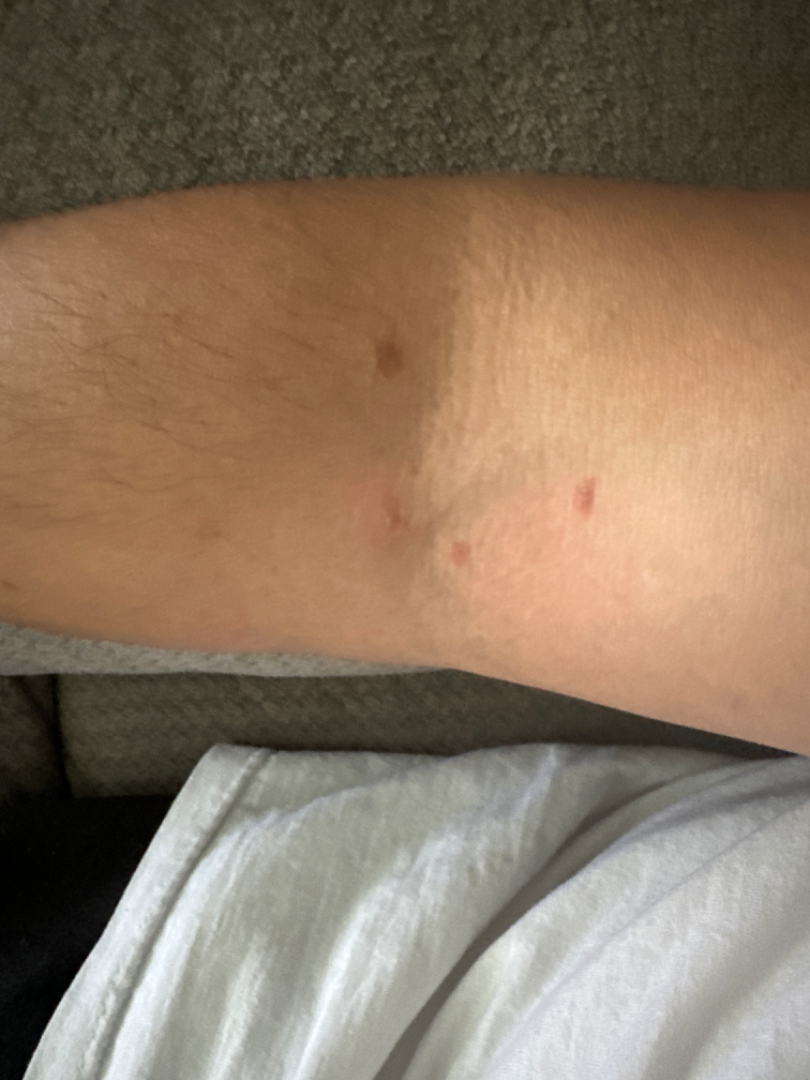The photograph was taken at a distance.
The contributor reports the lesion is rough or flaky and raised or bumpy.
No associated systemic symptoms reported.
The subject is 40–49, male.
Self-categorized by the patient as a rash.
Present for one to four weeks.
The affected area is the back of the torso, front of the torso and arm.
Symptoms reported: itching.
Fitzpatrick skin type II.
Favoring Acute constitutional eczema; an alternative is Infestation caused by Sarcoptes scabiei var bovis.